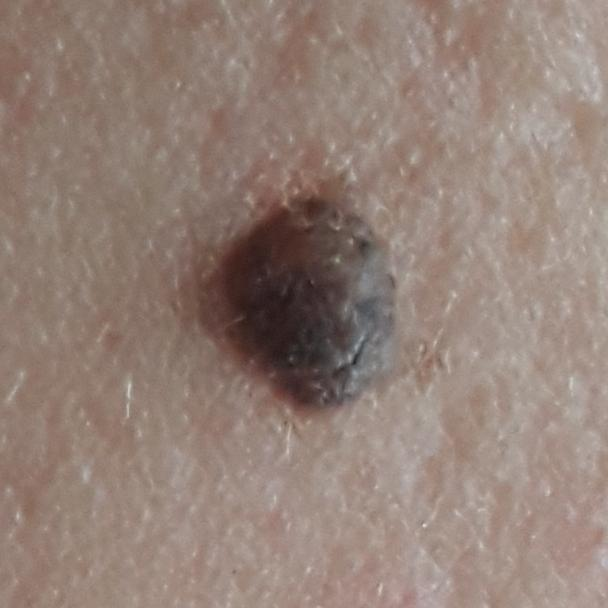Case:
• impression: nevus (clinical consensus)